A patient aged 66; a clinical close-up photograph of a skin lesion:
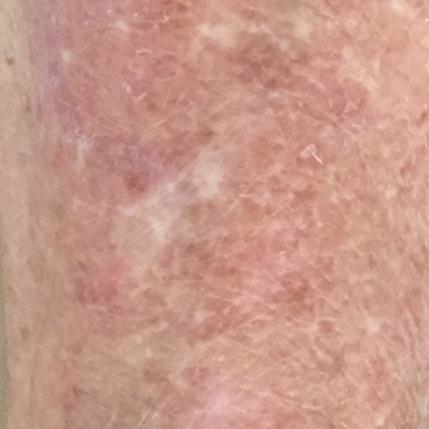Q: What is the anatomic site?
A: an arm
Q: What does the patient describe?
A: growth, itching
Q: What was the clinical impression?
A: actinic keratosis (clinical consensus)